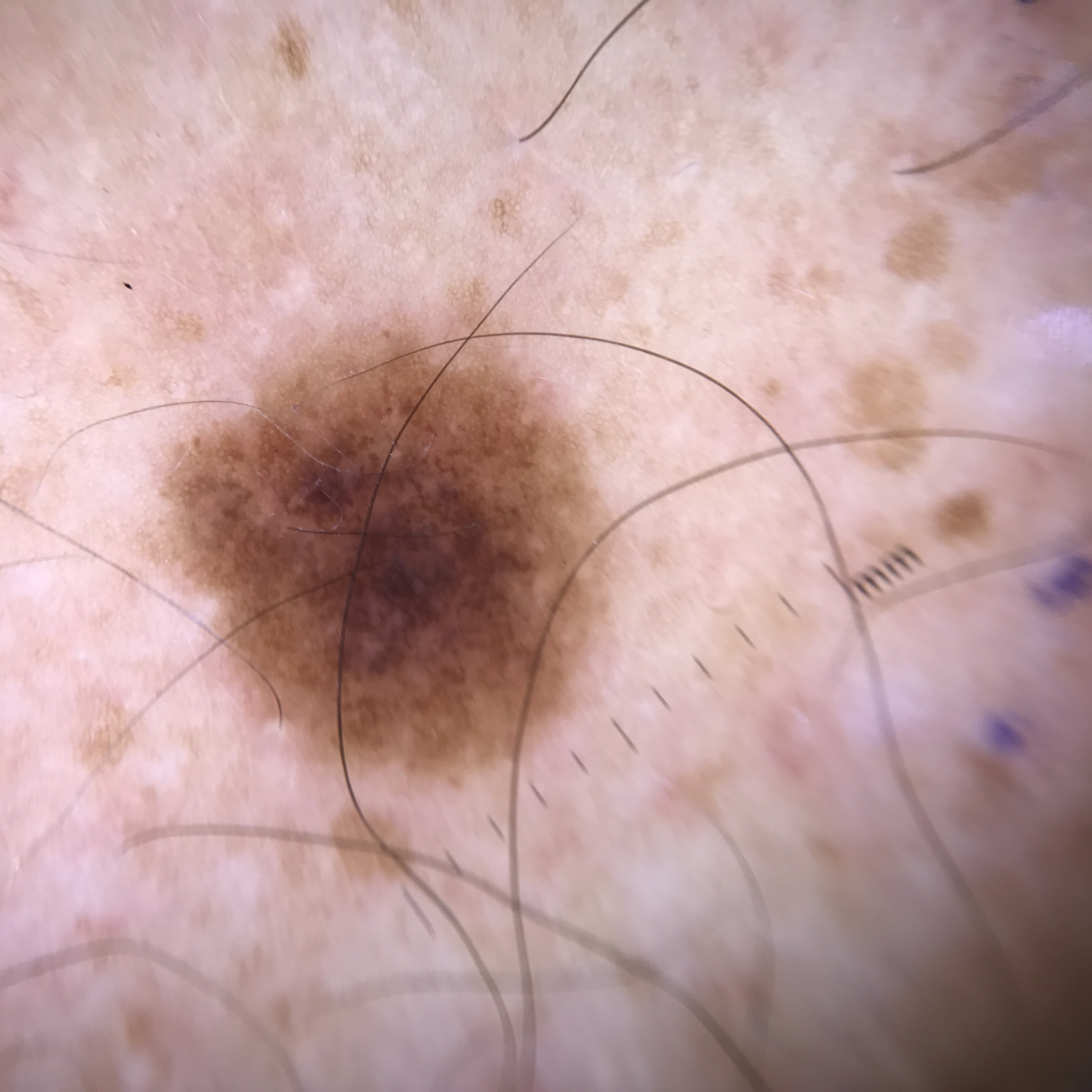image: dermatoscopy | assessment: dysplastic junctional nevus (expert consensus).